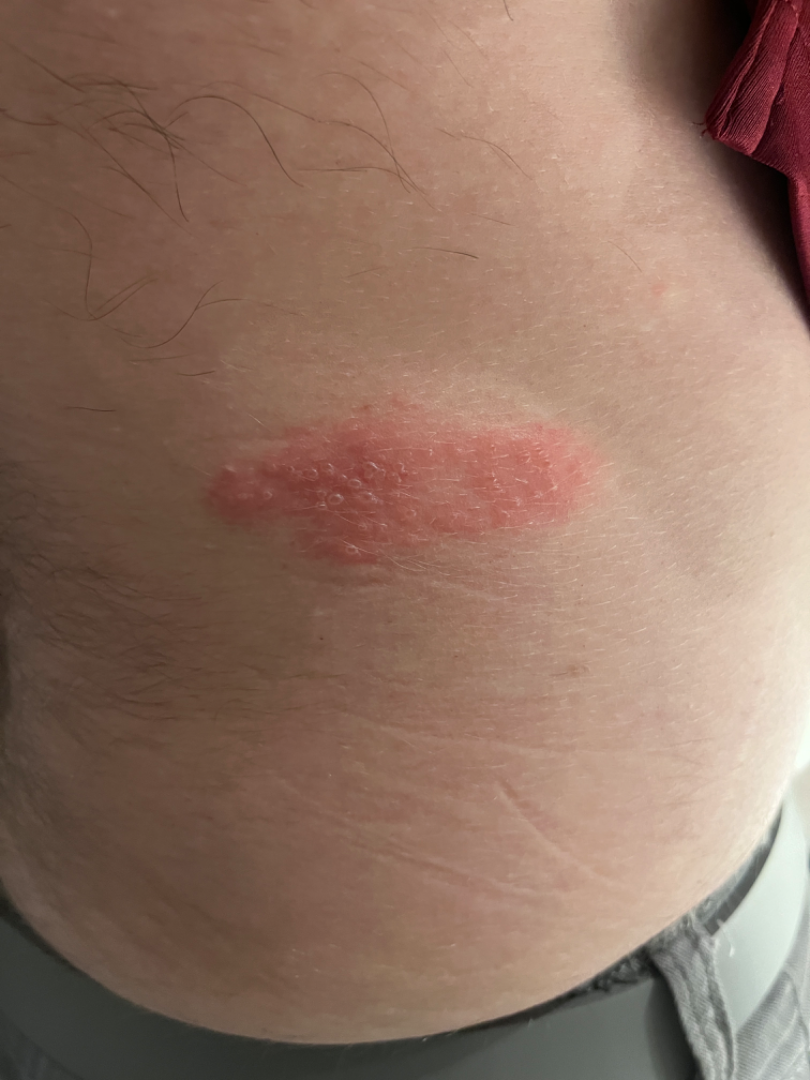The leading consideration is Herpes Zoster.